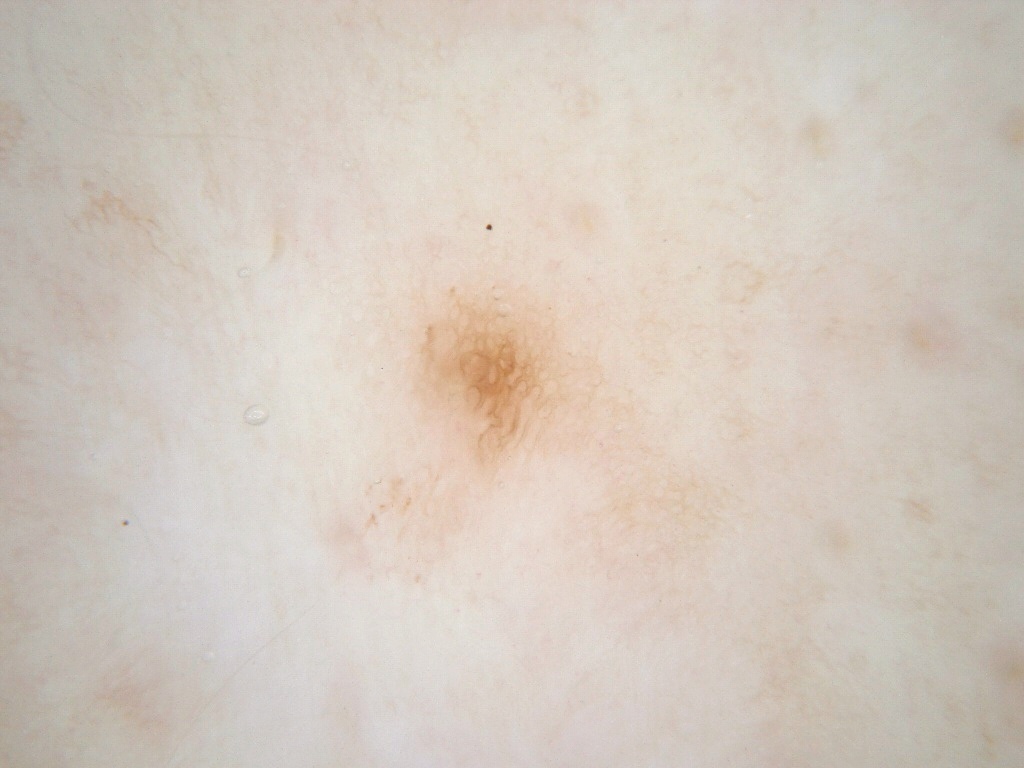Case summary:
* imaging · dermoscopic image
* patient · female, in their mid-40s
* dermoscopic pattern · pigment network; absent: negative network, streaks, milia-like cysts, and globules
* lesion bbox · 376, 270, 612, 492
* assessment · a melanocytic nevus, a benign skin lesion